Close-up view, located on the front of the torso: 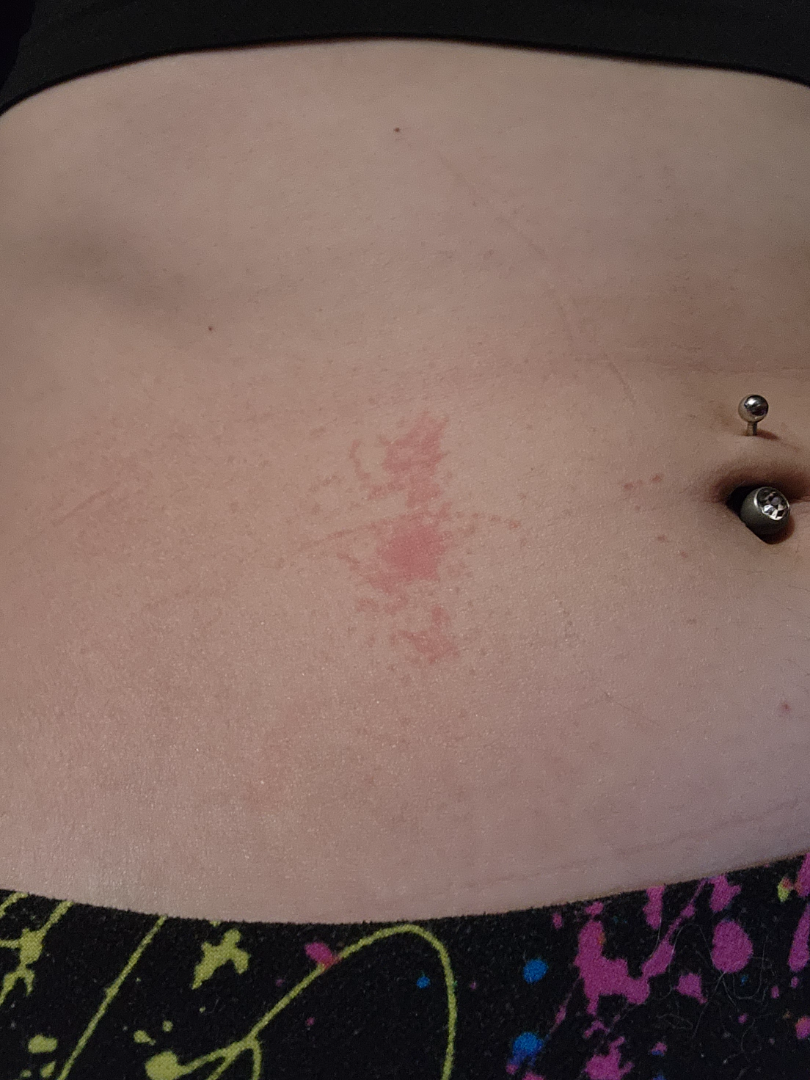<report>
  <differential>
    <leading>Allergic Contact Dermatitis</leading>
    <considered>Eczema</considered>
  </differential>
</report>